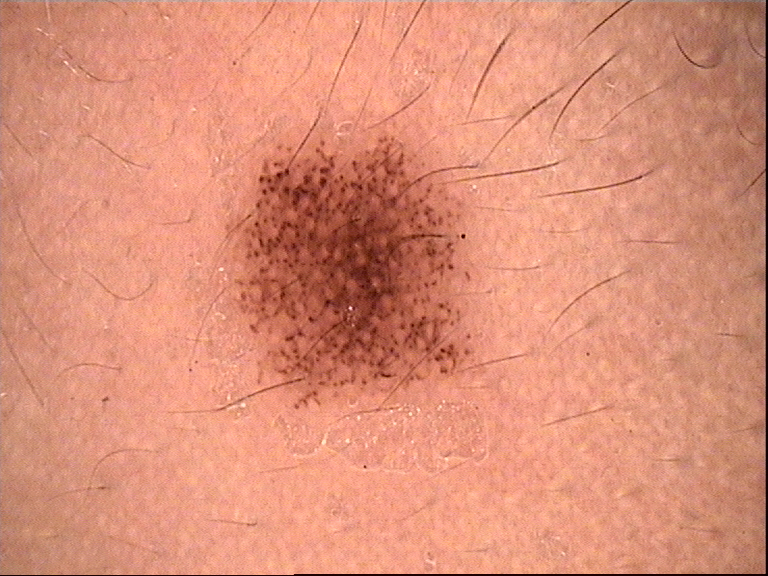Consistent with a junctional nevus.